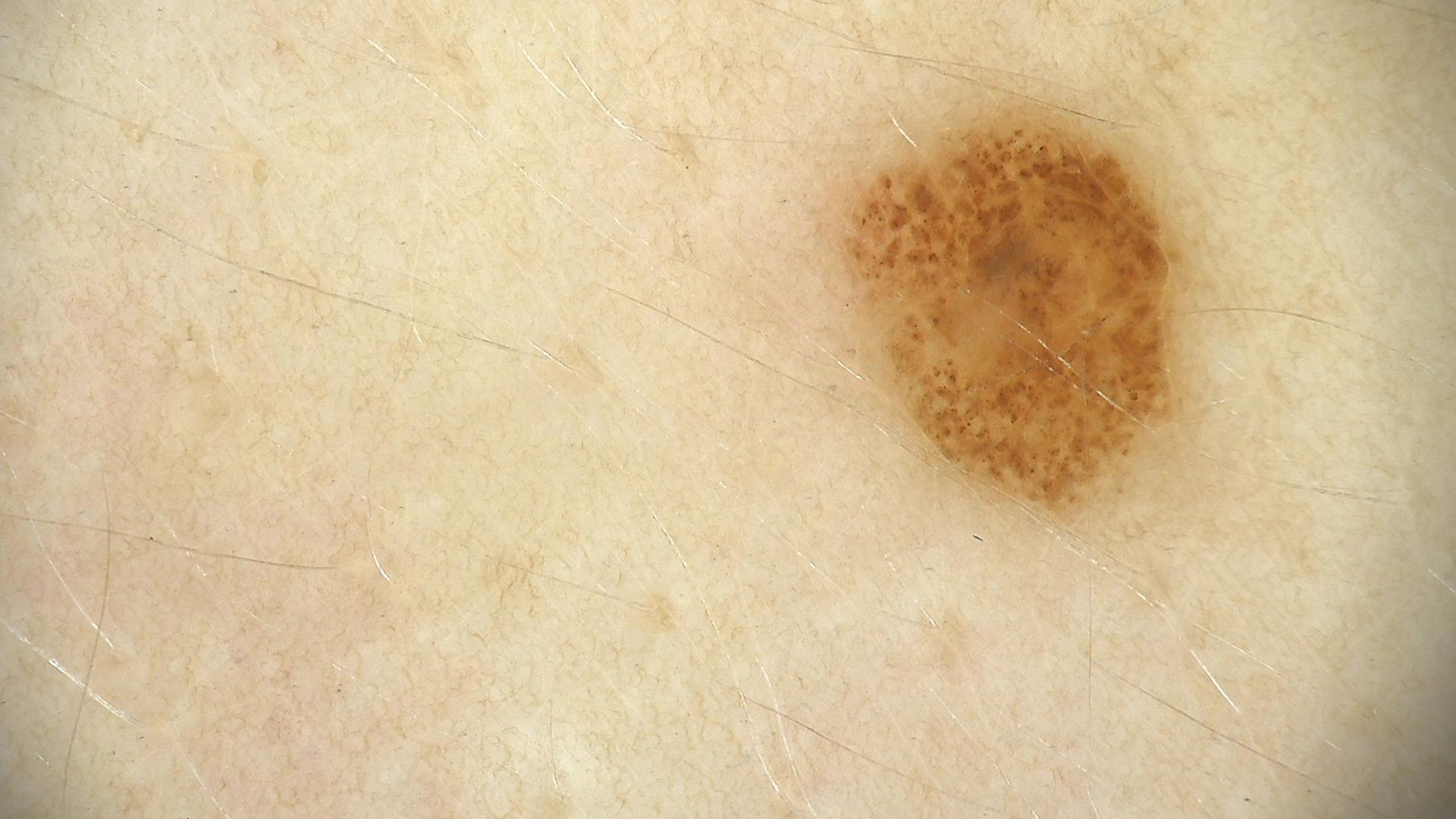  image: dermoscopy
  lesion_type:
    main_class: banal
    pattern: compound
  diagnosis:
    name: compound nevus
    code: cb
    malignancy: benign
    super_class: melanocytic
    confirmation: expert consensus